A dermoscopic image of a skin lesion.
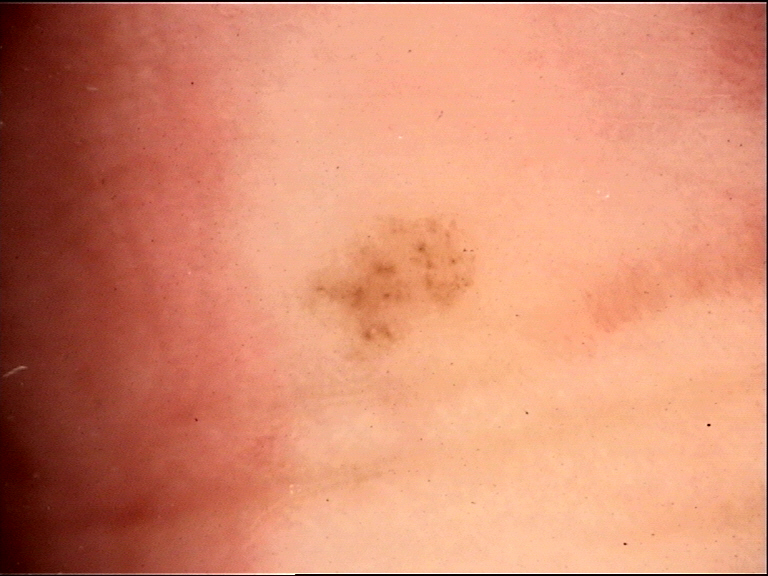diagnosis:
  name: acral dysplastic junctional nevus
  code: ajd
  malignancy: benign
  super_class: melanocytic
  confirmation: expert consensus